Self-categorized by the patient as a rash. This is a close-up image. The lesion is associated with itching, burning and enlargement. The patient reports the lesion is raised or bumpy. Located on the back of the hand, leg and top or side of the foot. Reported duration is less than one week. No relevant systemic symptoms: 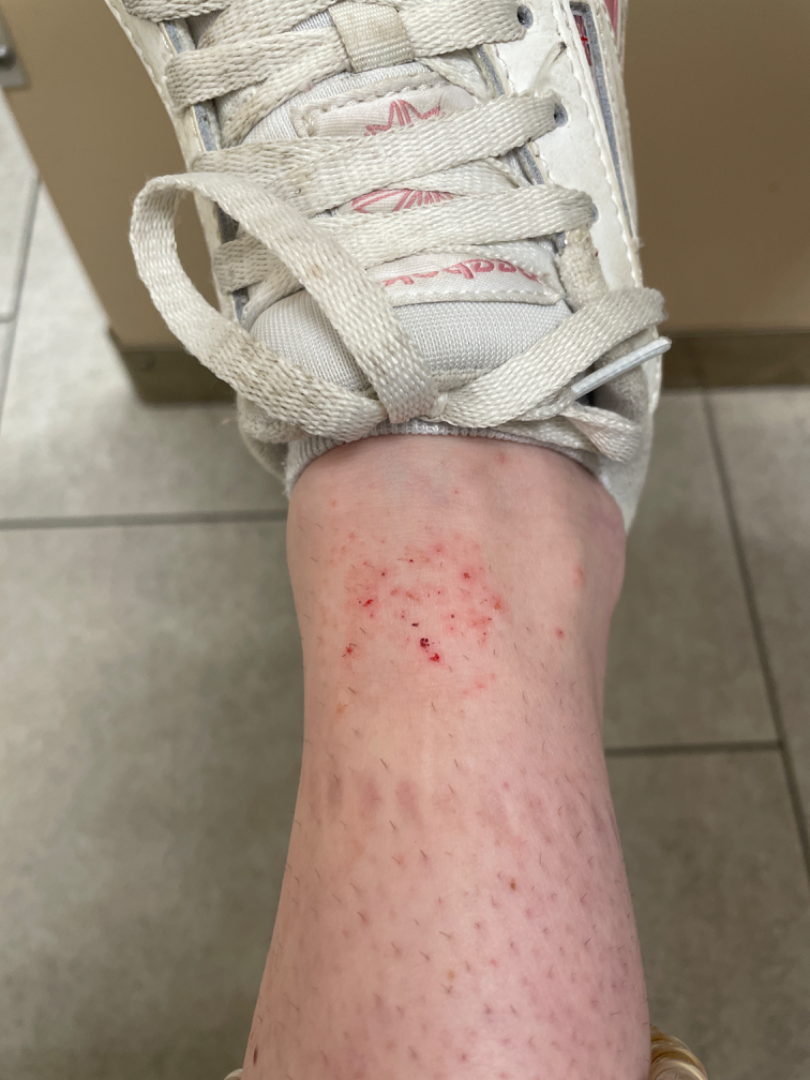Q: What conditions are considered?
A: favoring Superficial wound of body region; also consider Inflicted skin lesions; less likely is Irritant Contact Dermatitis